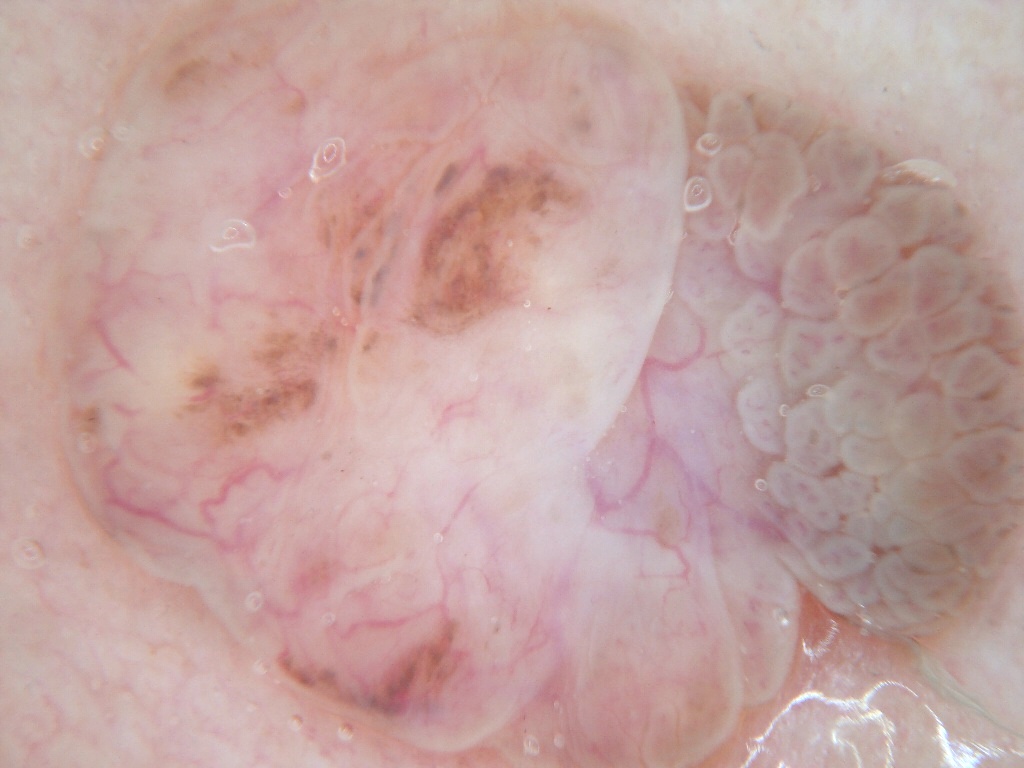imaging — dermoscopic image; lesion location — reaches across the whole image; impression — a benign skin lesion.